A male patient in their 70s — 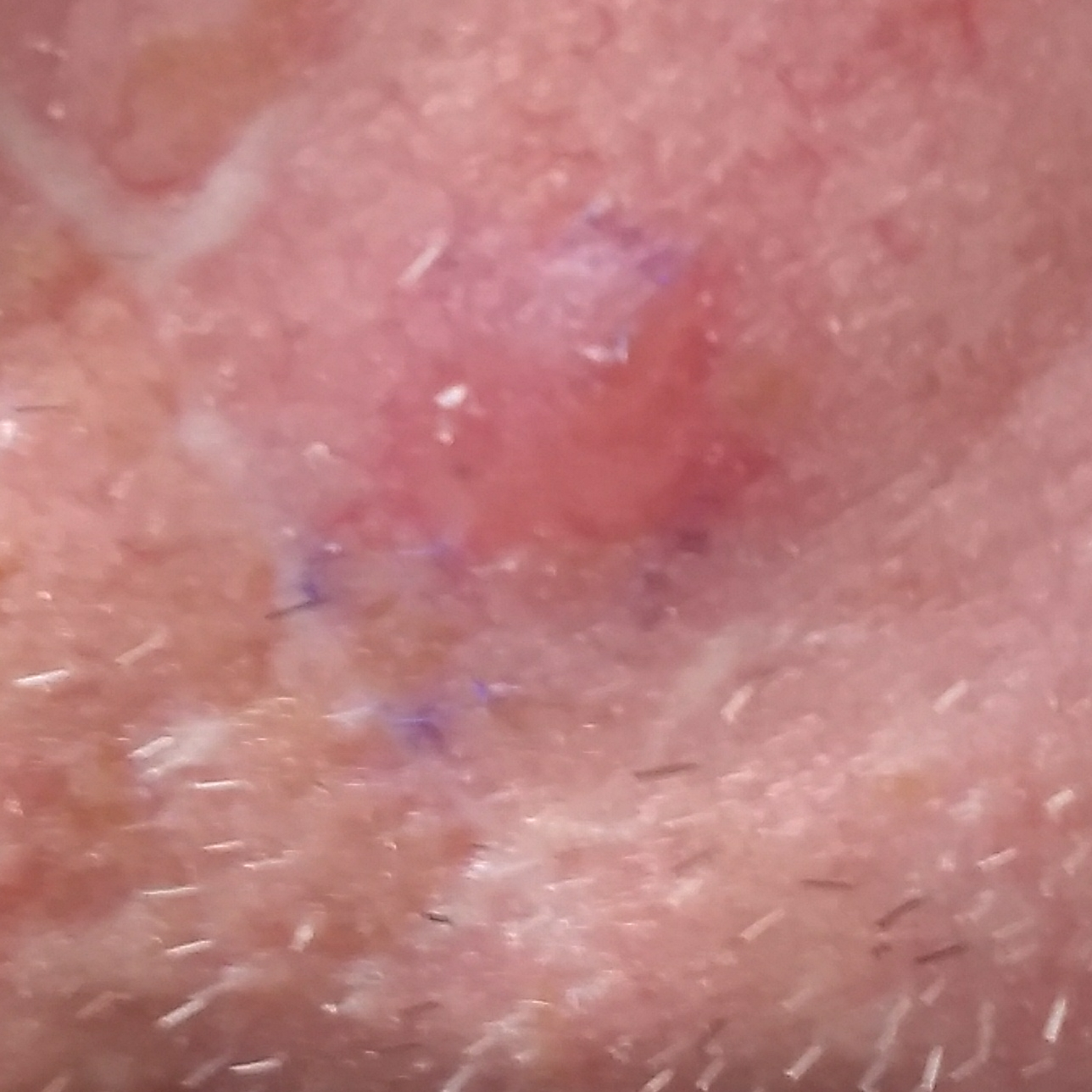Located on the face.
On biopsy, the diagnosis was a basal cell carcinoma.